A skin lesion imaged with a dermatoscope.
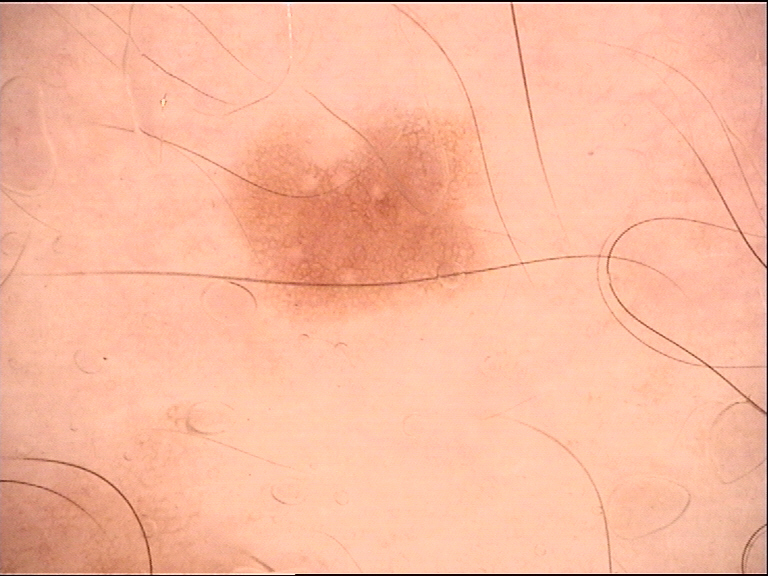The diagnosis was a dysplastic junctional nevus.